Reported duration is less than one week; close-up view — 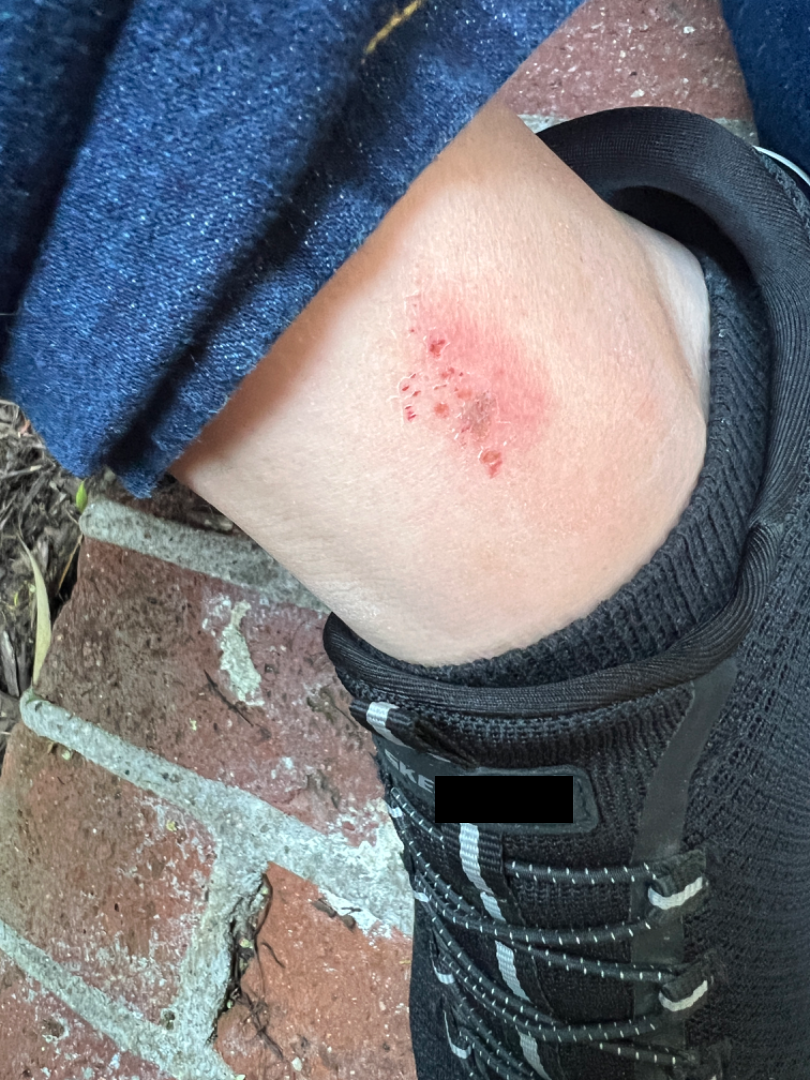On remote dermatologist review, the differential is split between Eczema and Irritant Contact Dermatitis.